Fitzpatrick phototype III; the patient described the issue as a rash; male patient, age 18–29; close-up view; the condition has been present for about one day; texture is reported as rough or flaky and flat; the lesion involves the back of the torso.
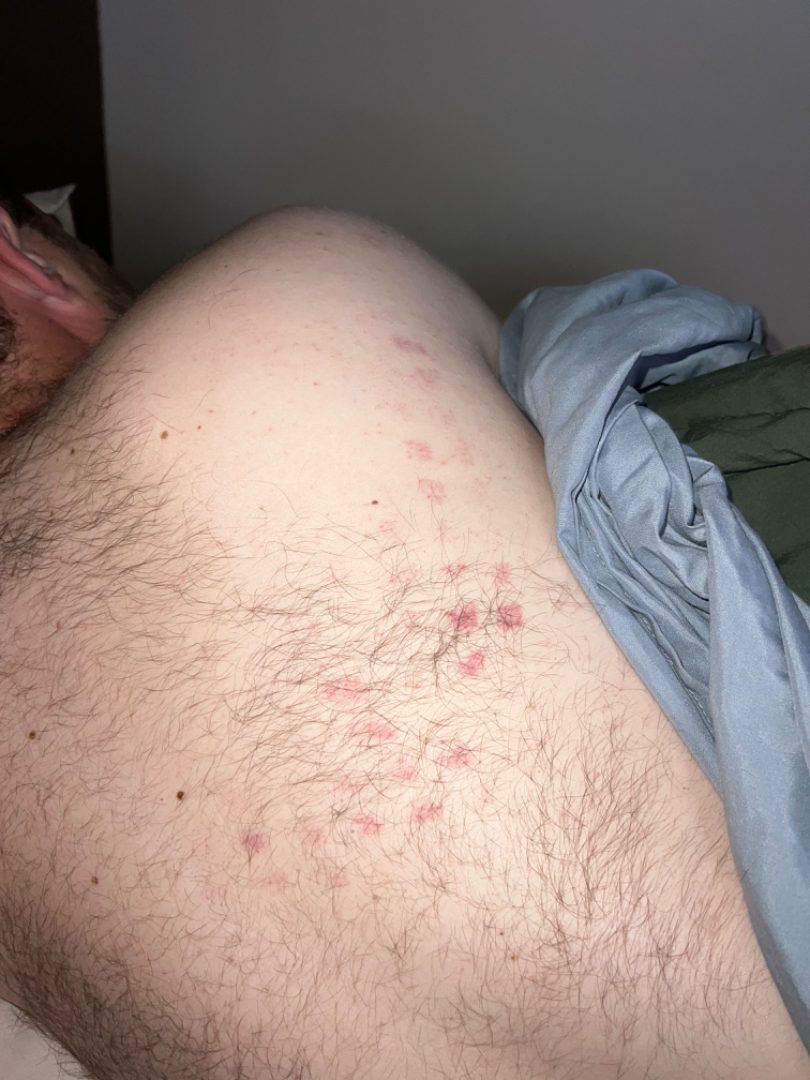Findings:
The skin findings could not be characterized from the image.